An image taken at an angle, the lesion involves the front of the torso and leg: 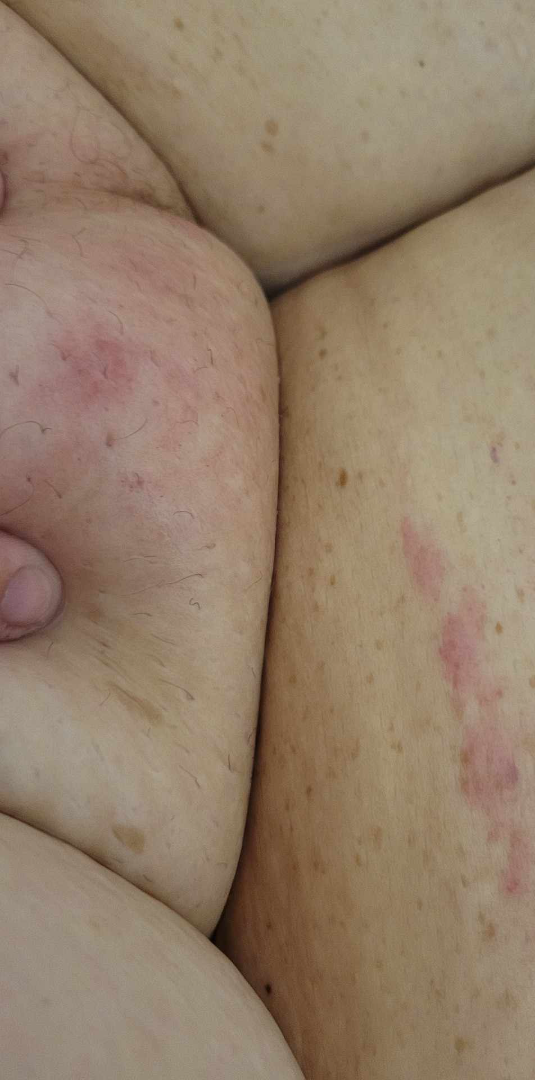Impression: The image was not sufficient for the reviewer to characterize the skin condition.